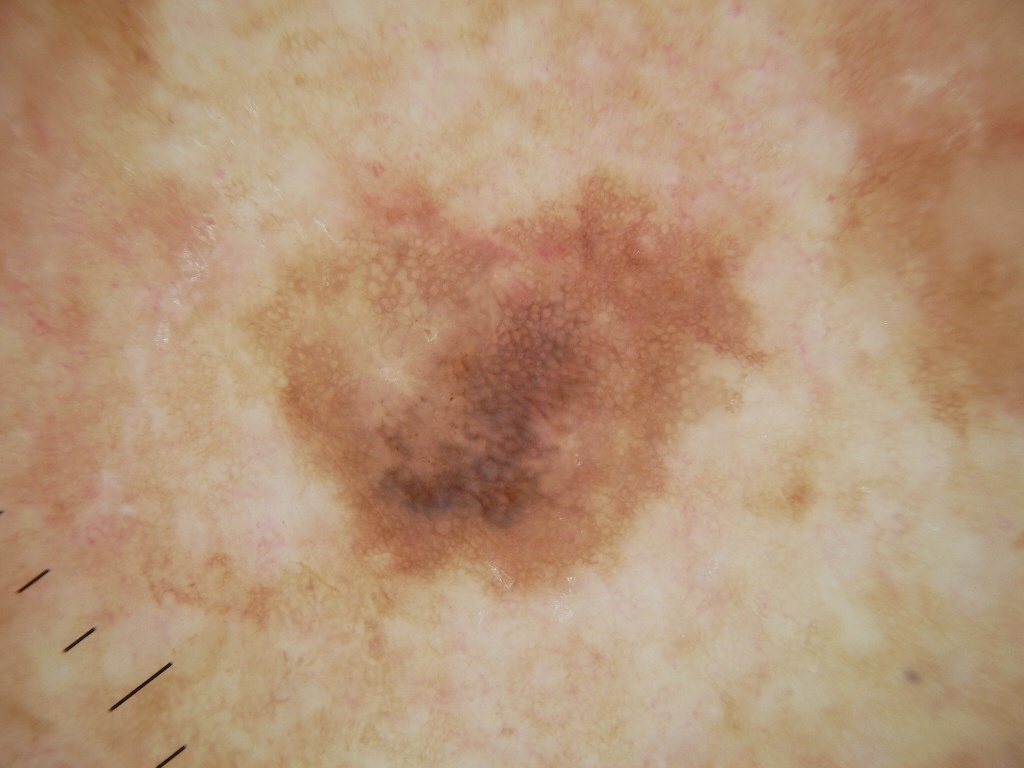Notes:
- subject — male, roughly 60 years of age
- image type — dermatoscopic image of a skin lesion
- size — ~18% of the field
- dermoscopic findings — pigment network
- lesion location — bbox=[245, 170, 766, 611]
- diagnosis — a melanoma